On a questionnaire the patient reported a personal history of skin cancer. The patient says their skin reddens with sun exposure. A skin lesion imaged with a dermatoscope. A female subject age 67: 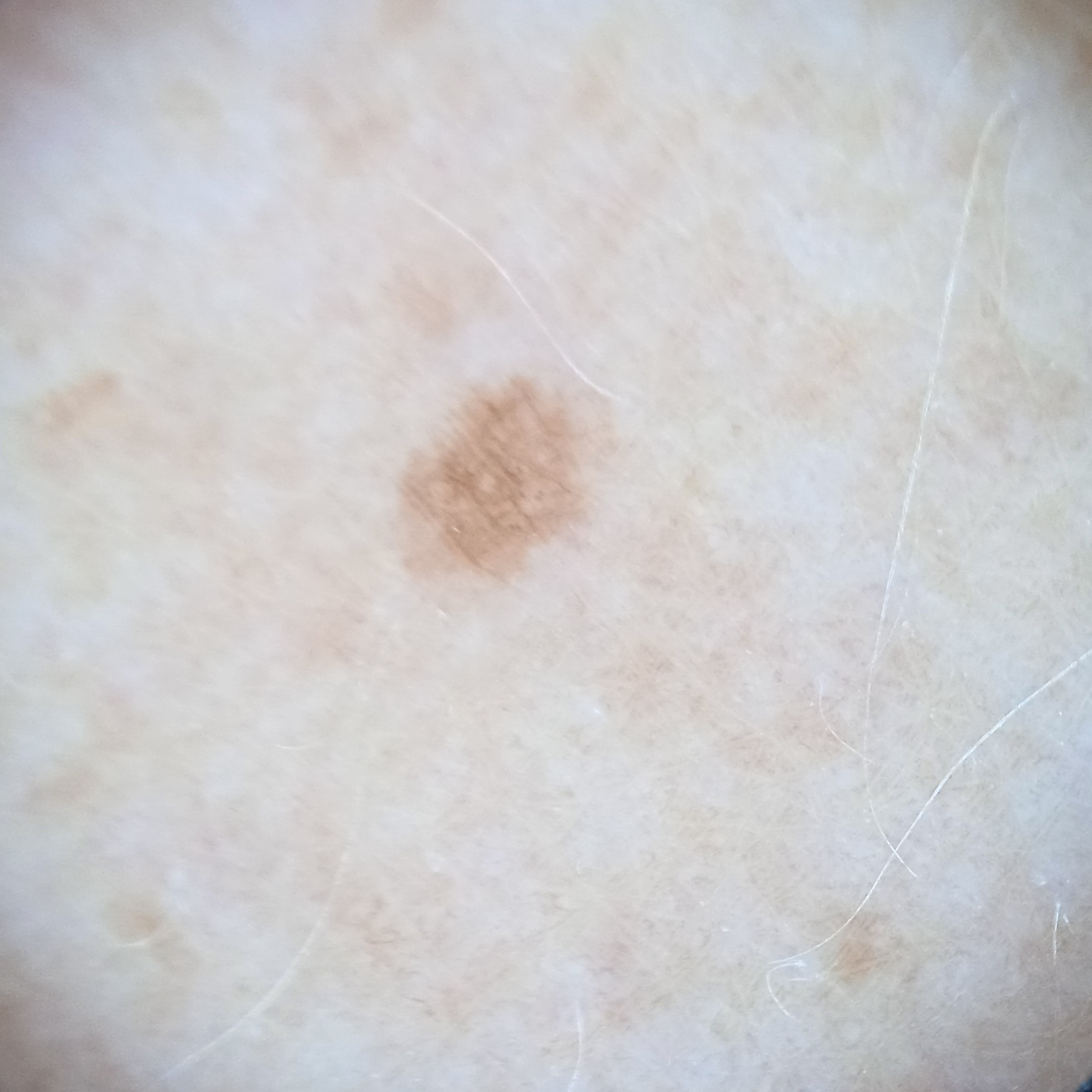The dermatologists' assessment was a melanocytic nevus.